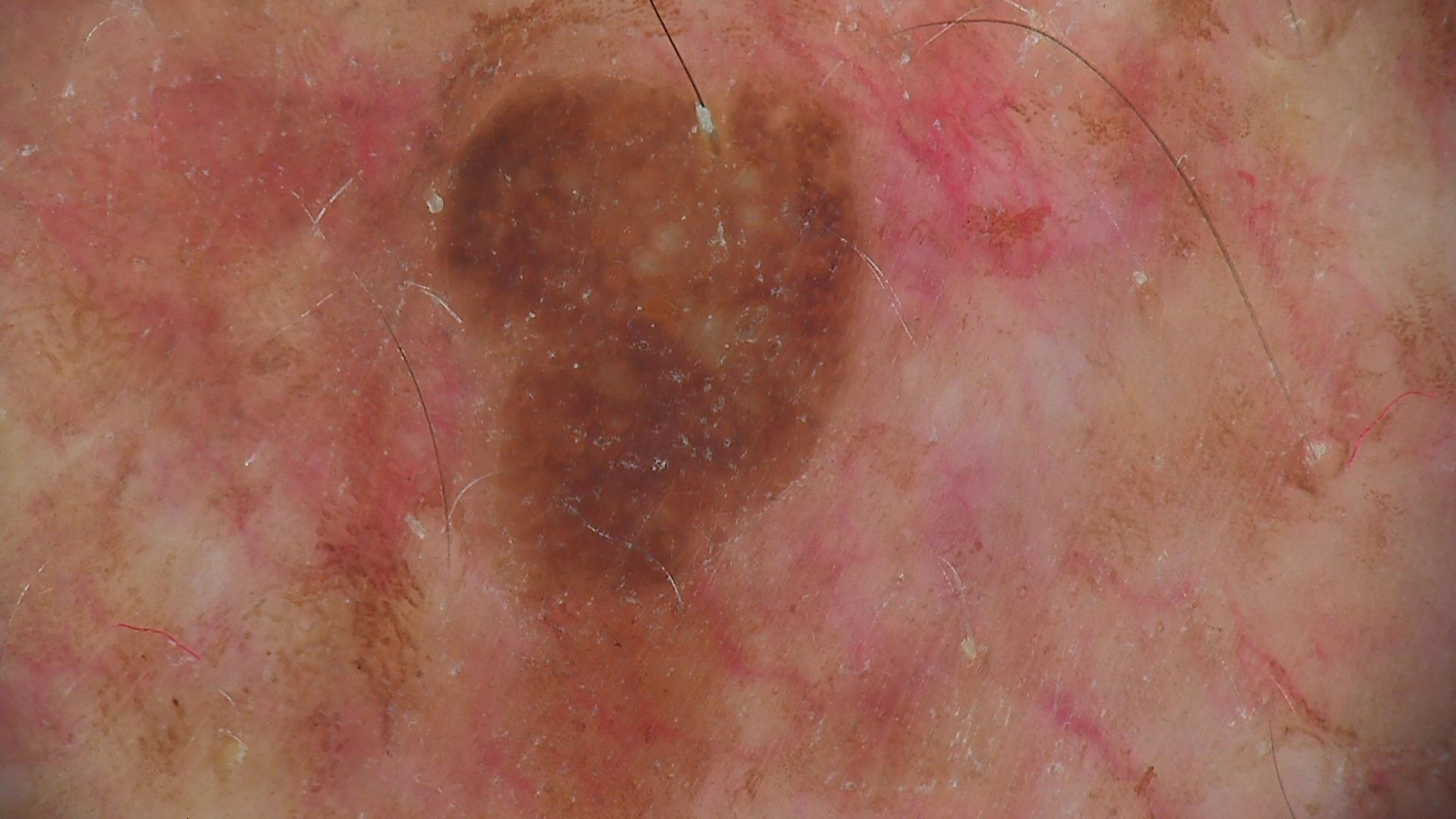Diagnosed as a keratinocytic, benign lesion — a seborrheic keratosis.